A female subject aged around 35 · this is a dermoscopic photograph of a skin lesion: 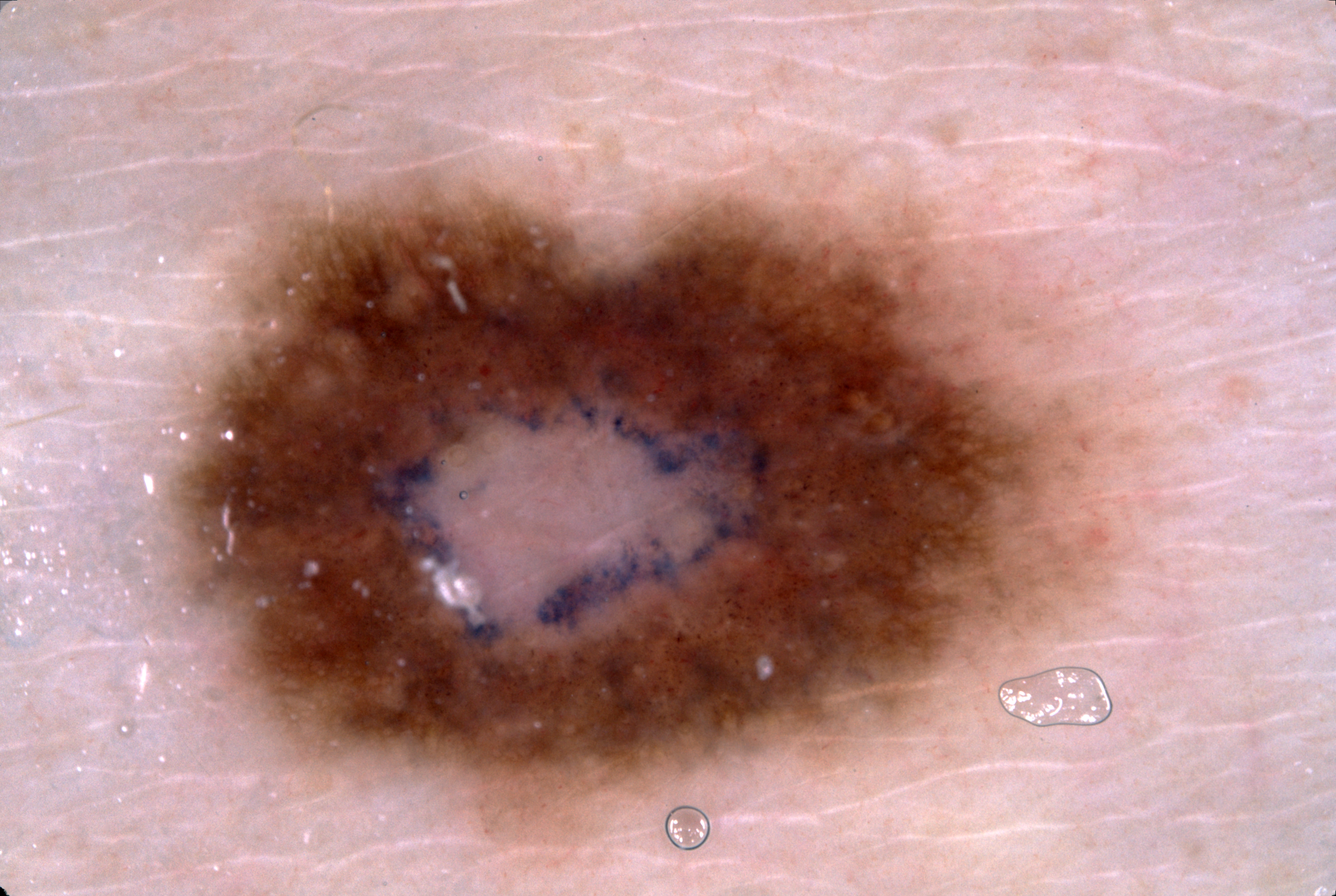Image and clinical context:
The lesion occupies roughly 36% of the field. Dermoscopically, the lesion shows milia-like cysts and pigment network; no negative network or streaks. With coordinates (x1, y1, x2, y2), the visible lesion spans box(168, 173, 1097, 830).
Assessment:
Clinically diagnosed as a melanocytic nevus.